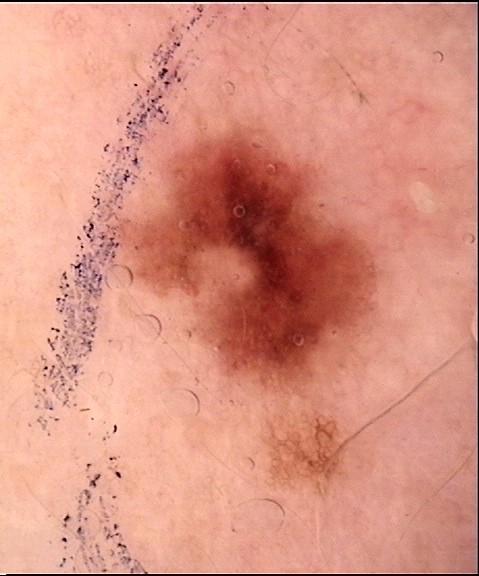Findings:
A skin lesion imaged with a dermatoscope.
Impression:
The diagnosis was a dysplastic junctional nevus.